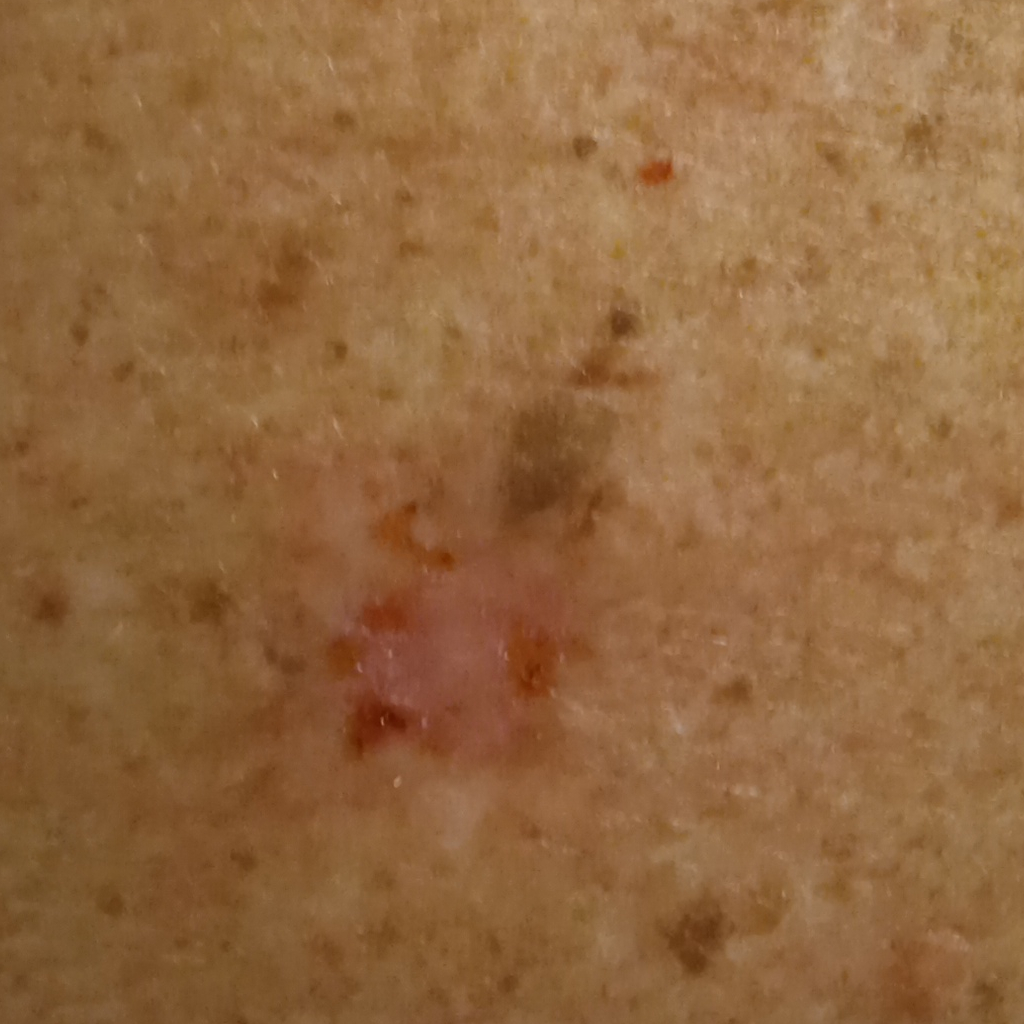Histopathology confirmed a basal cell carcinoma, following excision, with tumor thickness 3 mm.